A dermatoscopic image of a skin lesion: 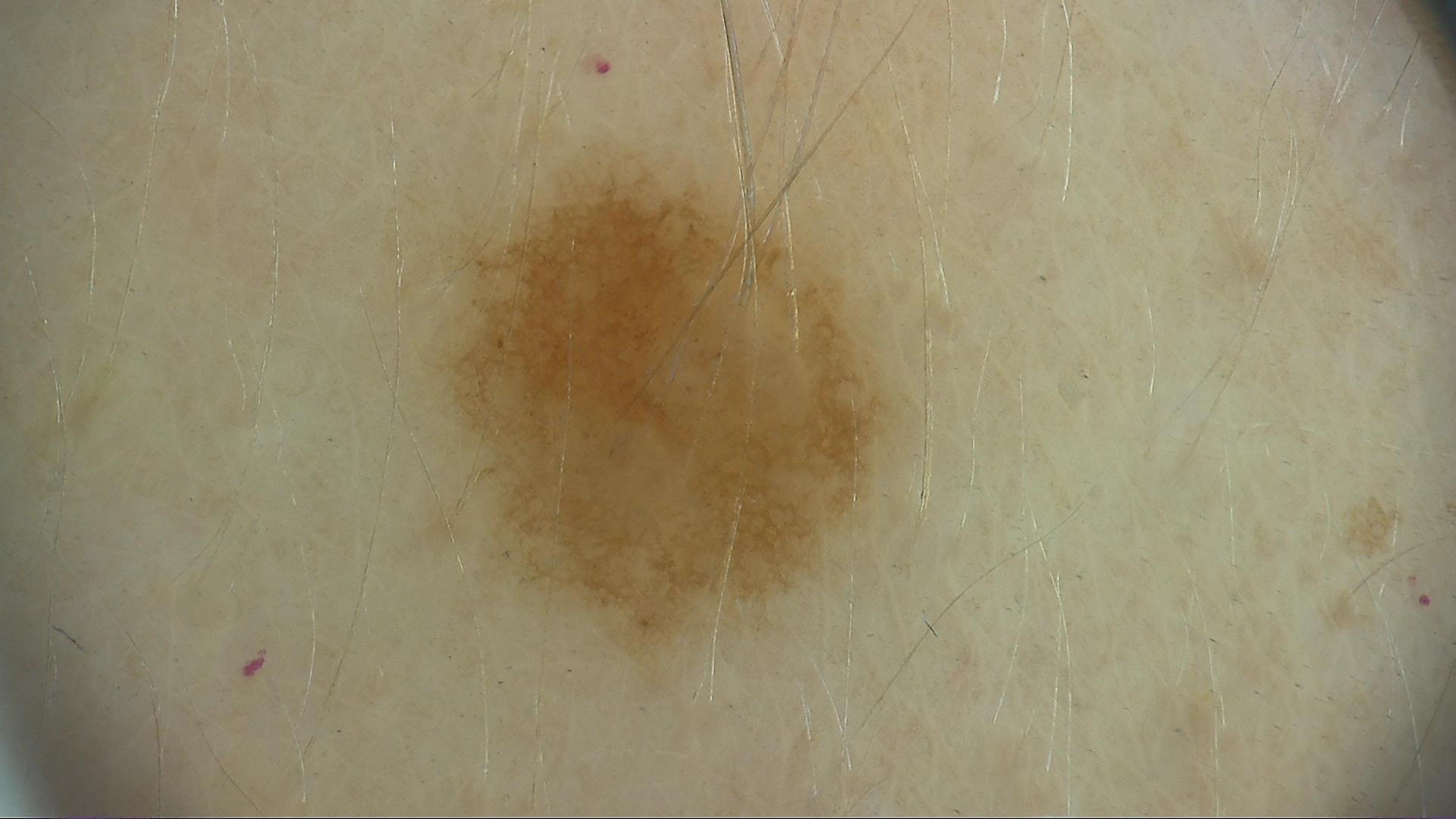Impression: Labeled as a benign lesion — a dysplastic junctional nevus.